Present for less than one week; texture is reported as raised or bumpy; the arm is involved; self-categorized by the patient as a rash; the patient reported no systemic symptoms; the photo was captured at a distance; FST III:
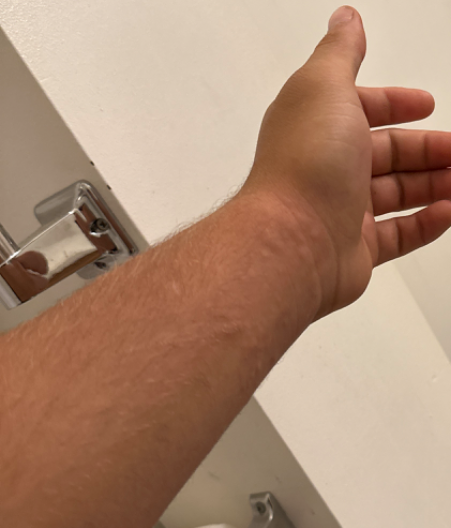dermatologist impression = most likely Urticaria; also consider Insect Bite; the differential also includes Allergic Contact Dermatitis.